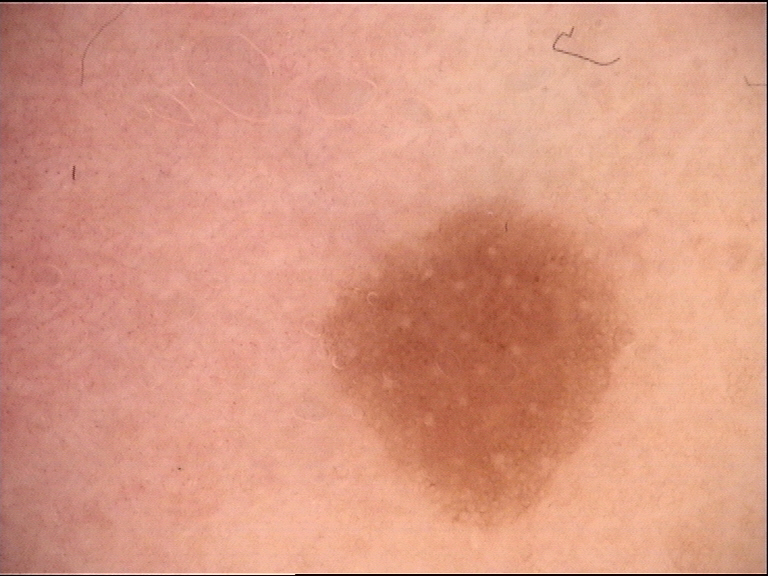Case: A dermoscopic image of a skin lesion. Conclusion: Labeled as a benign lesion — a dysplastic junctional nevus.